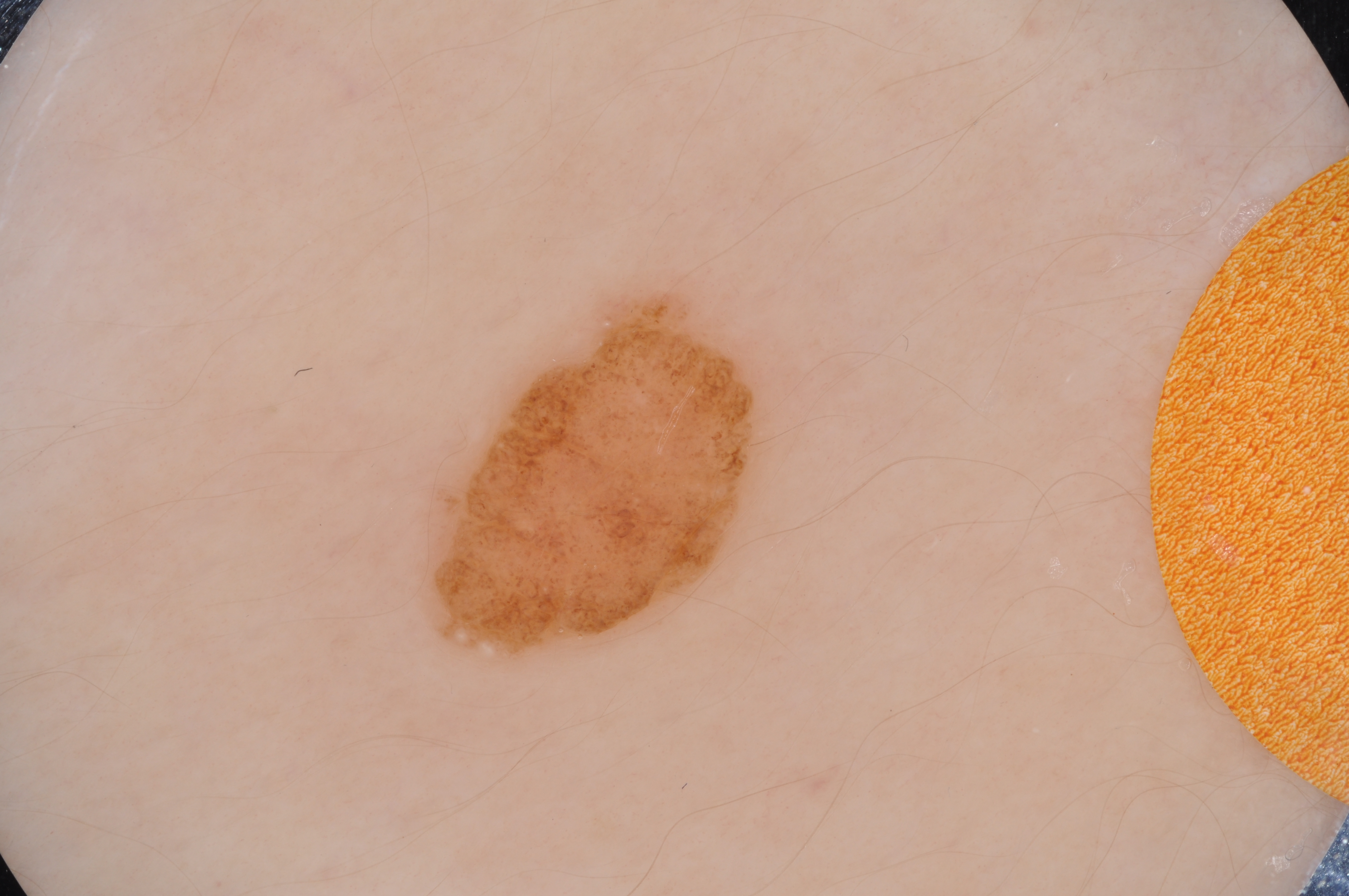The patient is a male aged around 15. Dermoscopy of a skin lesion. As (left, top, right, bottom), the lesion occupies the region 429, 293, 760, 663. The dermoscopic pattern shows milia-like cysts. The diagnostic assessment was a melanocytic nevus, a benign skin lesion.